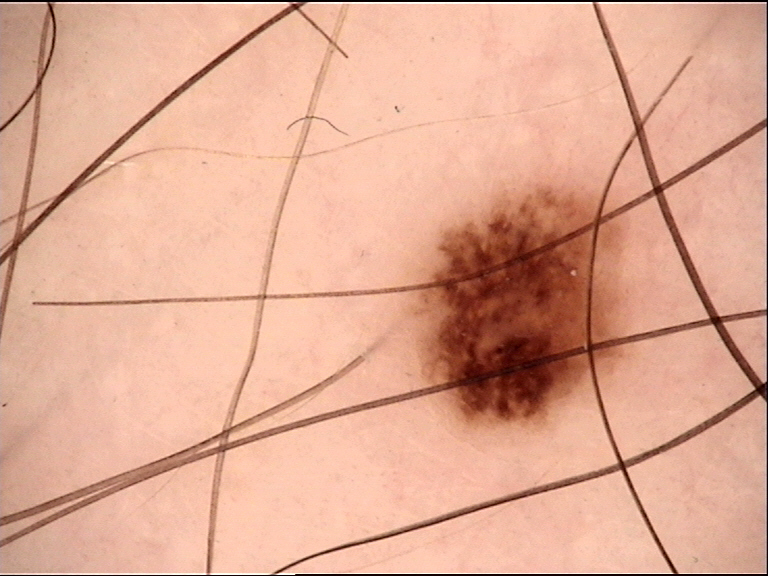The diagnostic label was a dysplastic junctional nevus.